Close-up view — 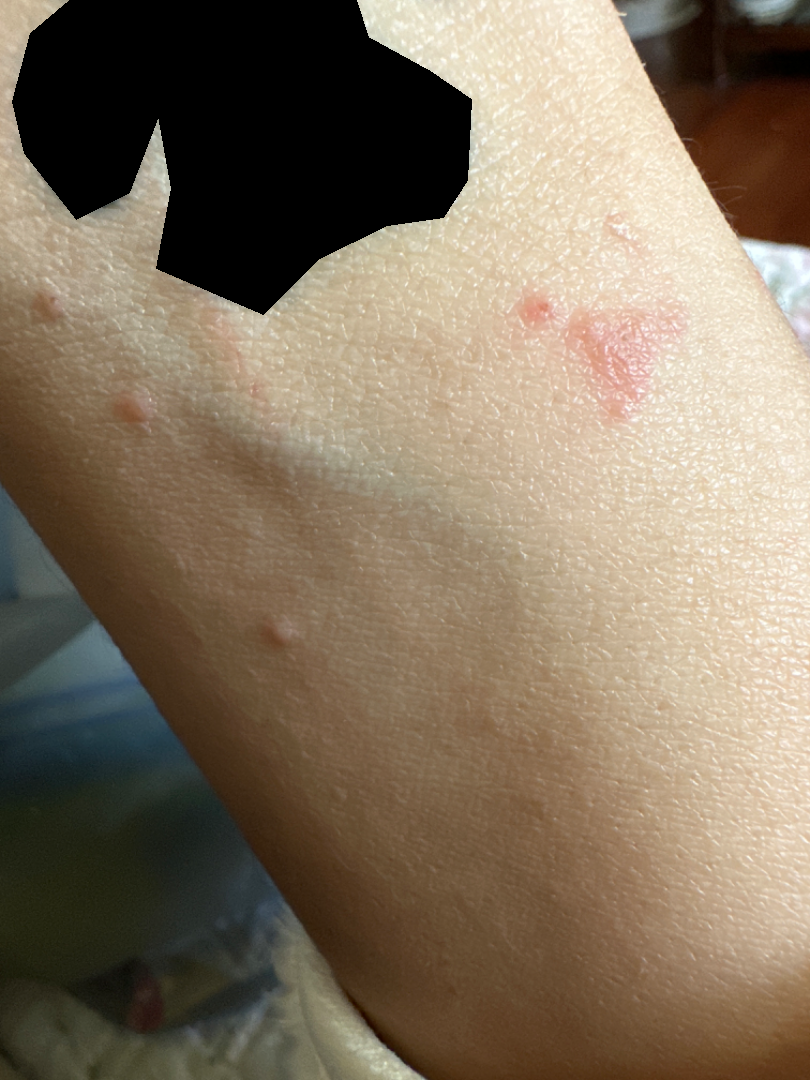History: Skin tone: Fitzpatrick II; lay reviewers estimated Monk skin tone scale 2 or 3. Impression: On remote dermatologist review, Allergic Contact Dermatitis (0.67); Eczema (0.33).